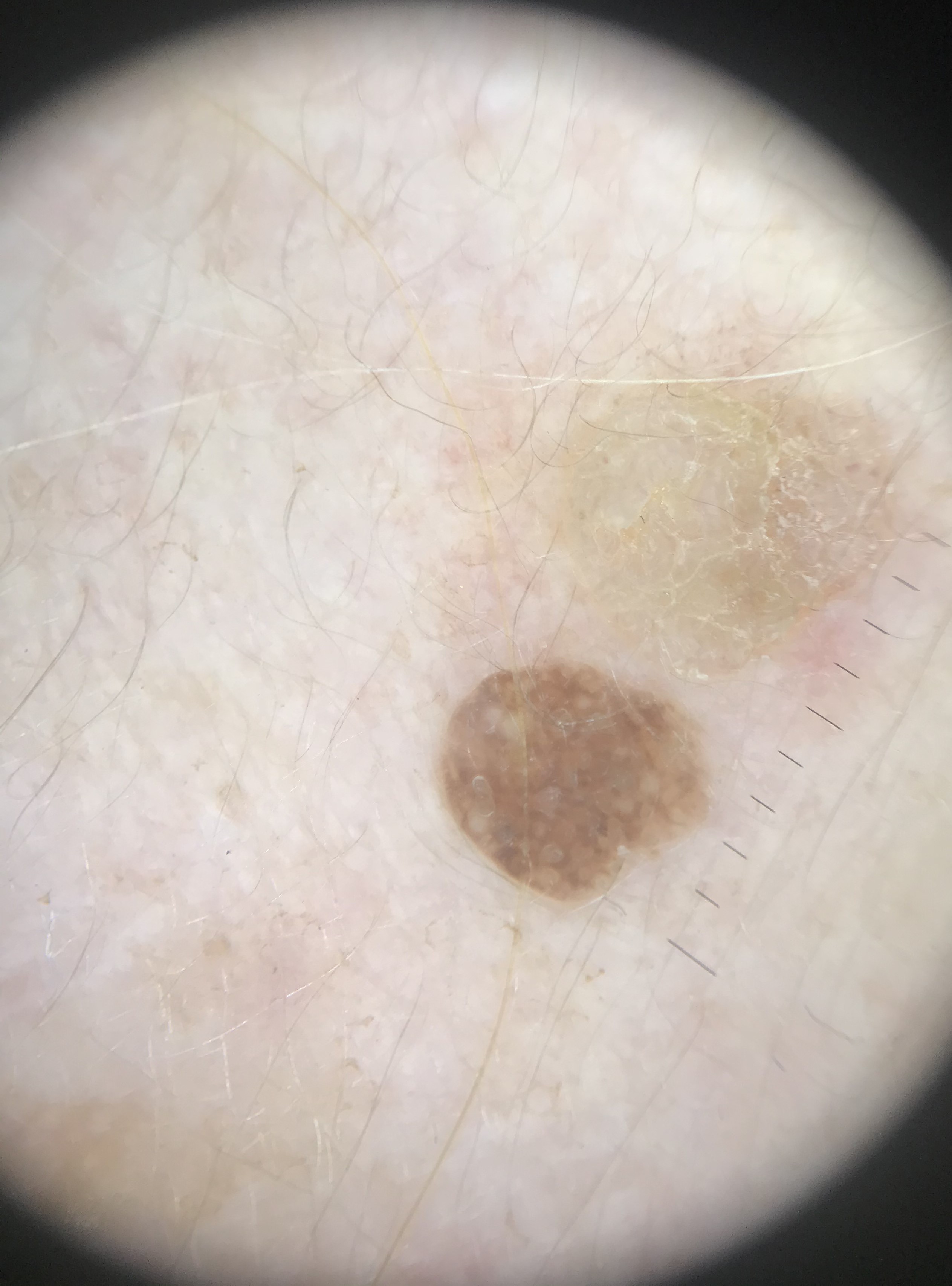Q: What is the imaging modality?
A: dermoscopy
Q: What kind of lesion is this?
A: keratinocytic
Q: What is the diagnosis?
A: seborrheic keratosis (expert consensus)